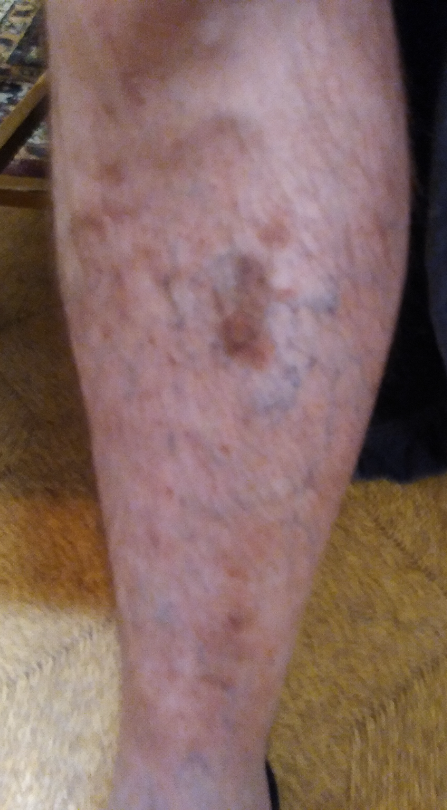{
  "duration": "more than one year",
  "body_site": "leg",
  "patient": "male, age 60–69",
  "shot_type": "at a distance",
  "differential": {
    "leading": [
      "Pigmented purpuric eruption"
    ]
  }
}